The photograph was taken at a distance · the affected area is the leg: 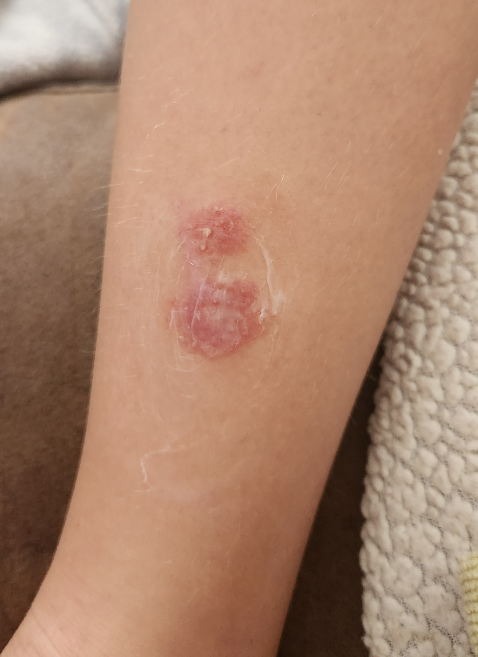No differential diagnosis could be assigned on photographic review. The condition has been present for less than one week. Reported lesion symptoms include itching. Texture is reported as raised or bumpy and fluid-filled. The patient described the issue as a rash. The patient reported no systemic symptoms.